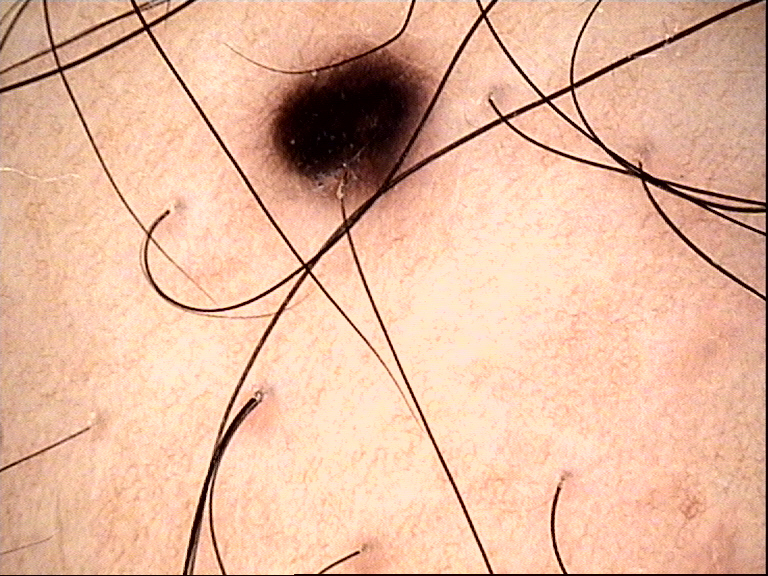Consistent with a benign lesion — a dysplastic junctional nevus.